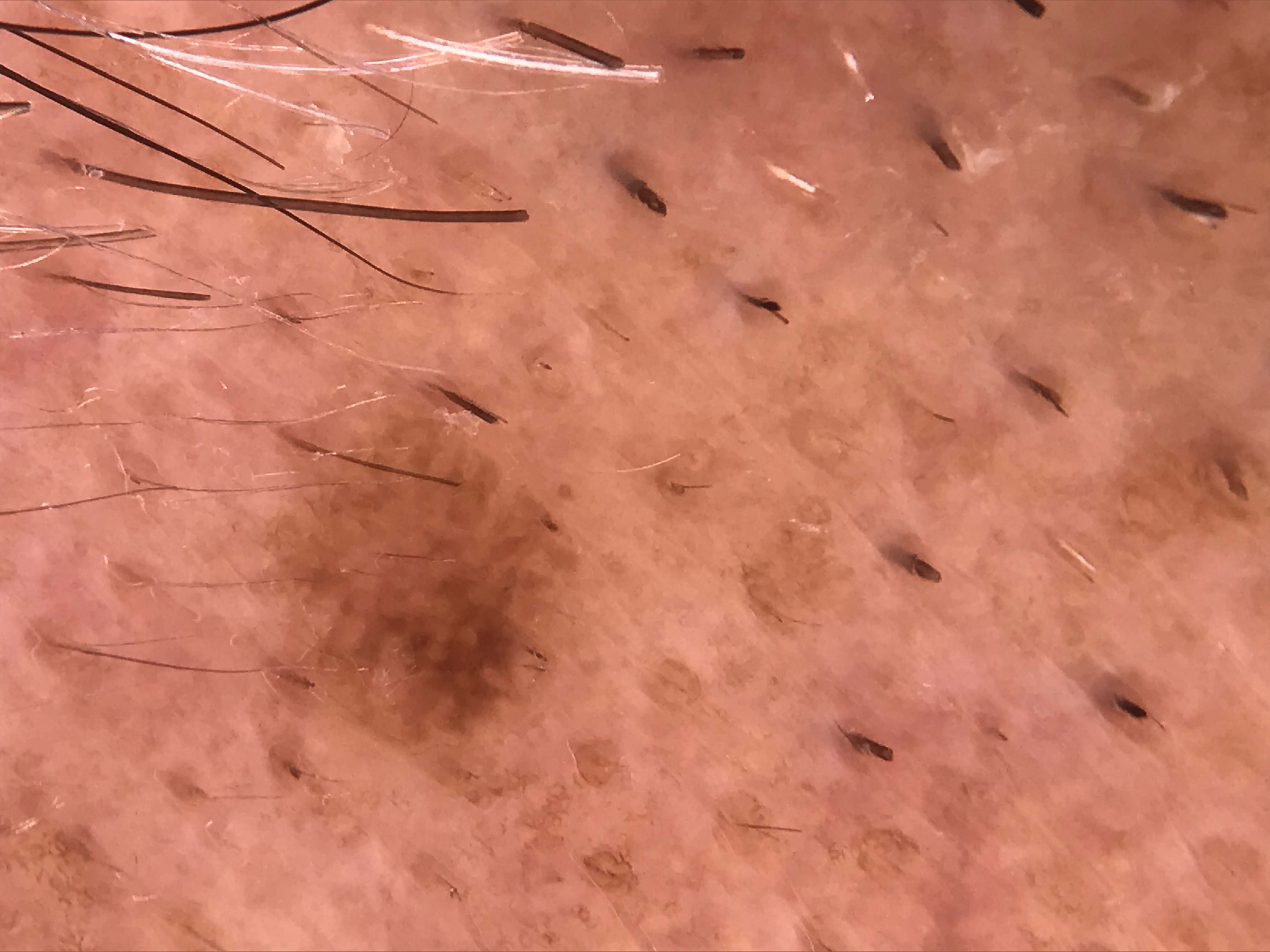Diagnosed as a seborrheic keratosis.